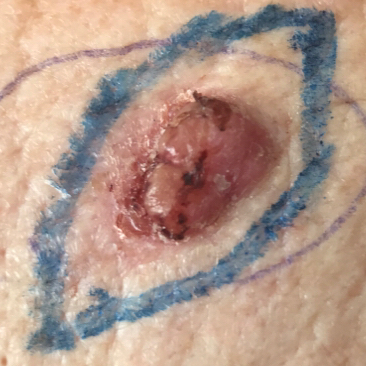A female patient in their late 70s. A clinical close-up photograph of a skin lesion. The patient was assessed as Fitzpatrick phototype I. The lesion is on the neck. The patient describes that the lesion itches and is elevated, but has not bled and does not hurt. Confirmed on histopathology as a skin cancer — a basal cell carcinoma.